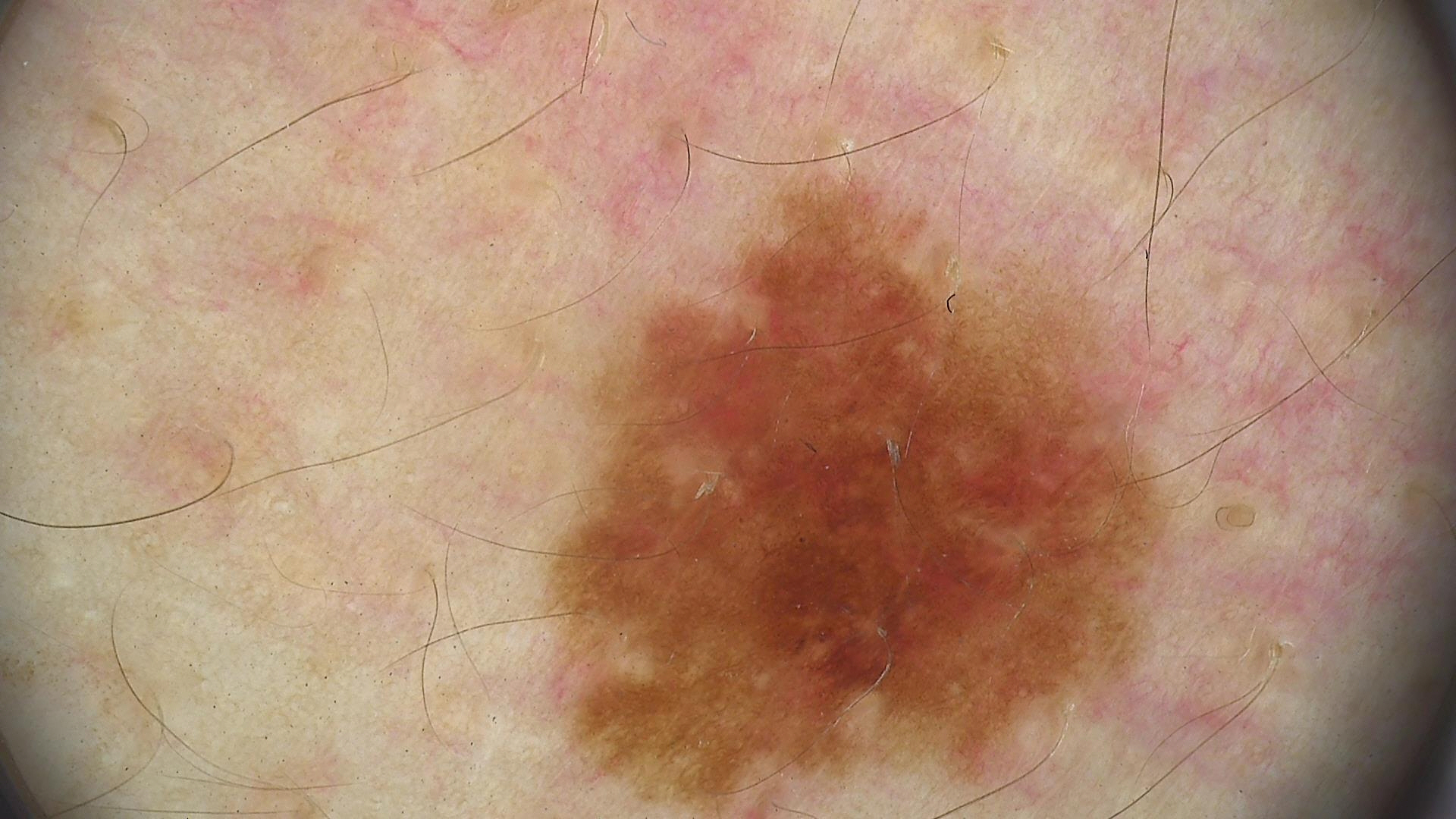Impression:
The diagnosis was a benign lesion — a dysplastic junctional nevus.